The photograph was taken at an angle · Fitzpatrick II; lay reviewers estimated Monk Skin Tone 2: 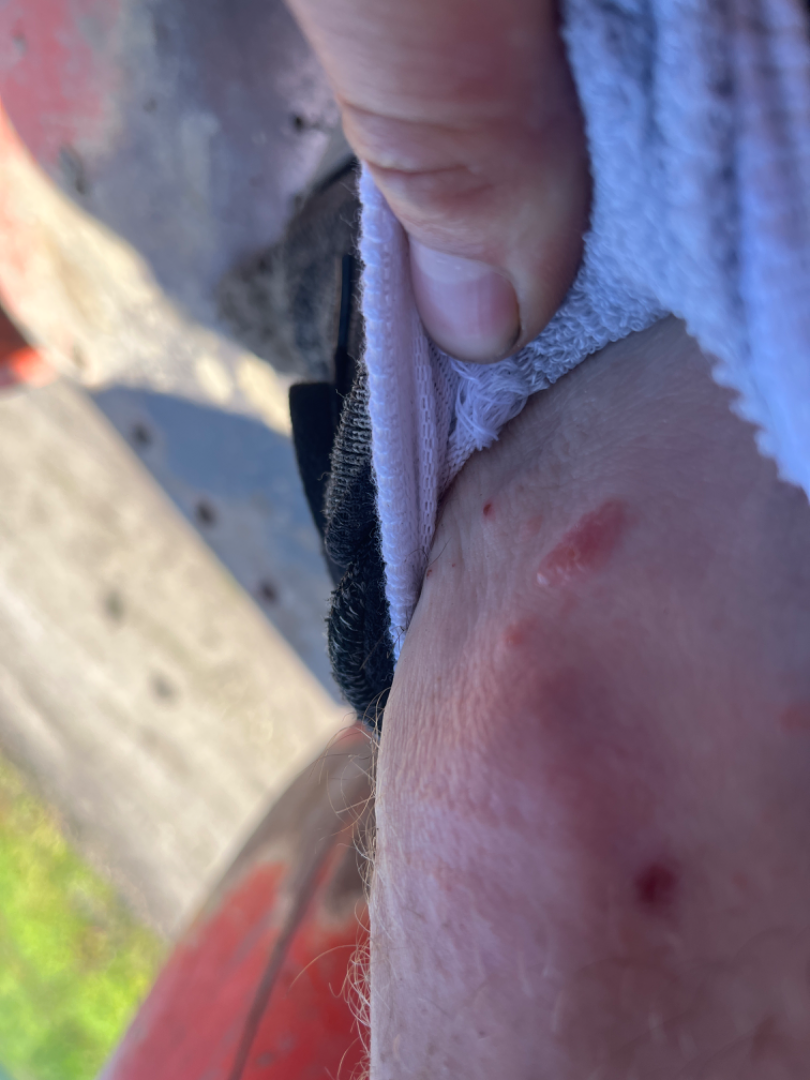The skin condition could not be confidently assessed from this image.